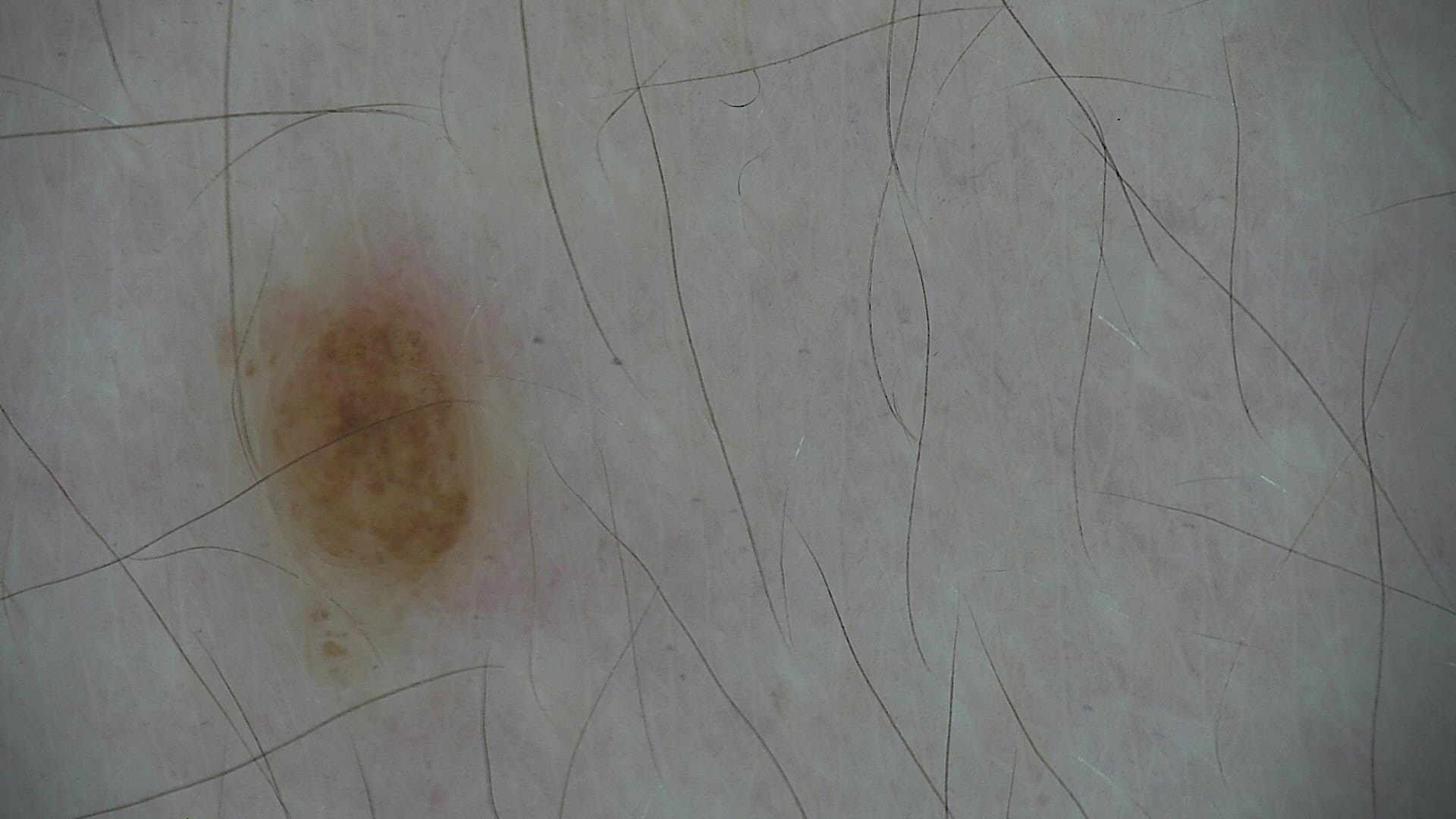A dermoscopic image of a skin lesion.
The morphology is that of a banal lesion.
Consistent with a compound nevus.